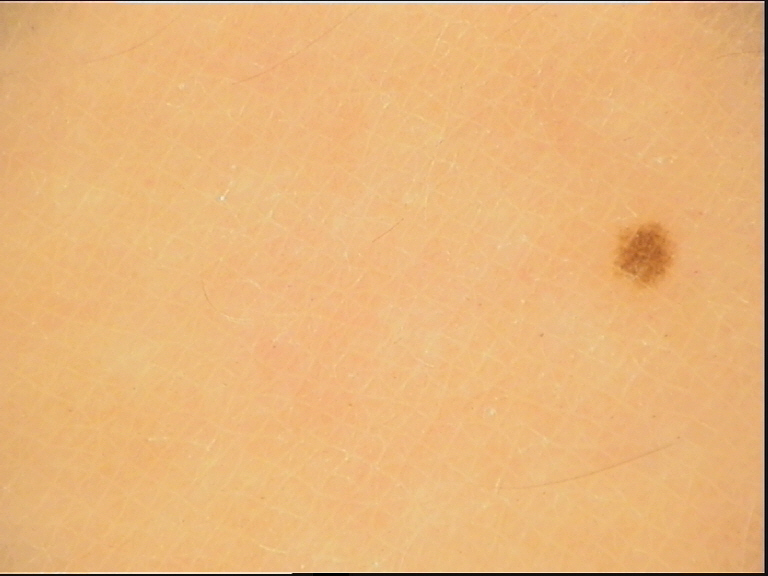image=dermatoscopy; label=dysplastic junctional nevus (expert consensus).